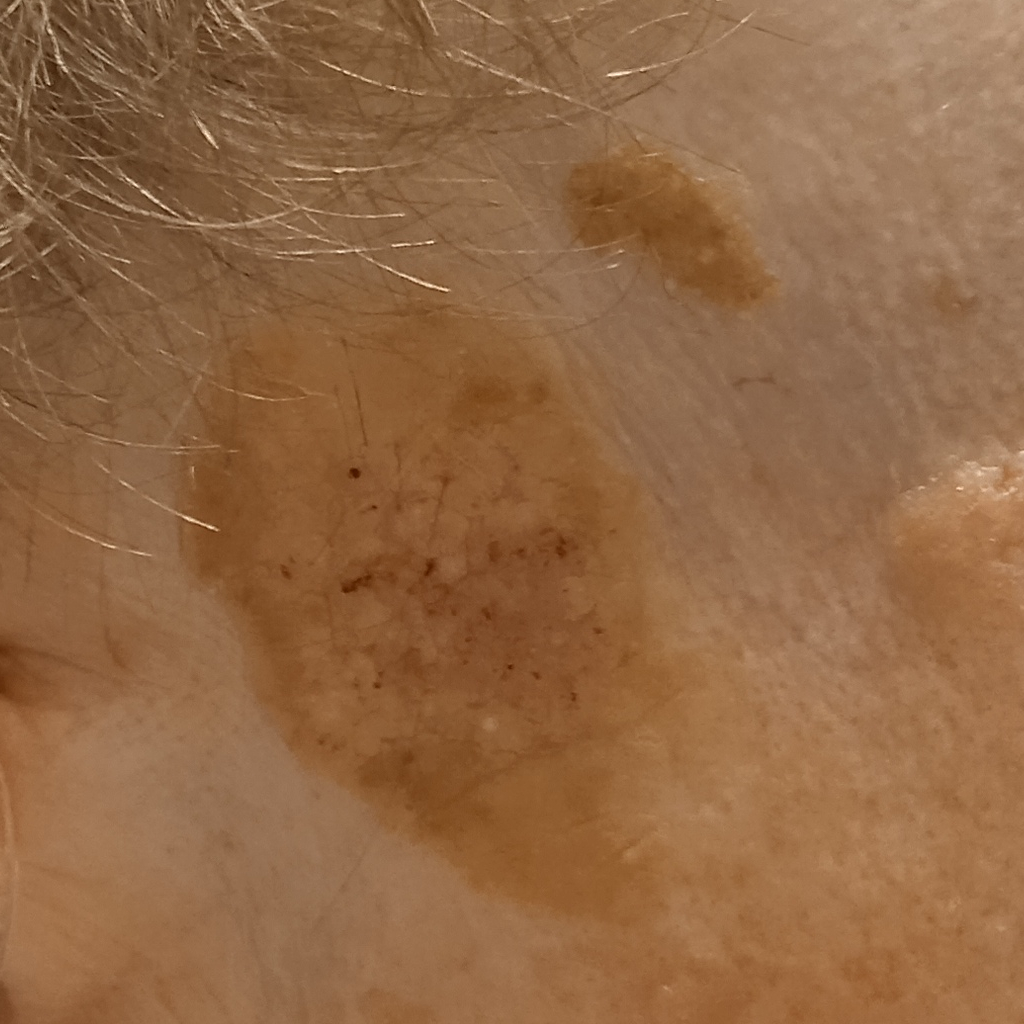sun reaction=skin reddens painfully with sun exposure; nevus count=a moderate number of melanocytic nevi; image=clinical photograph; size=36.6 mm; diagnosis=seborrheic keratosis (dermatologist consensus).